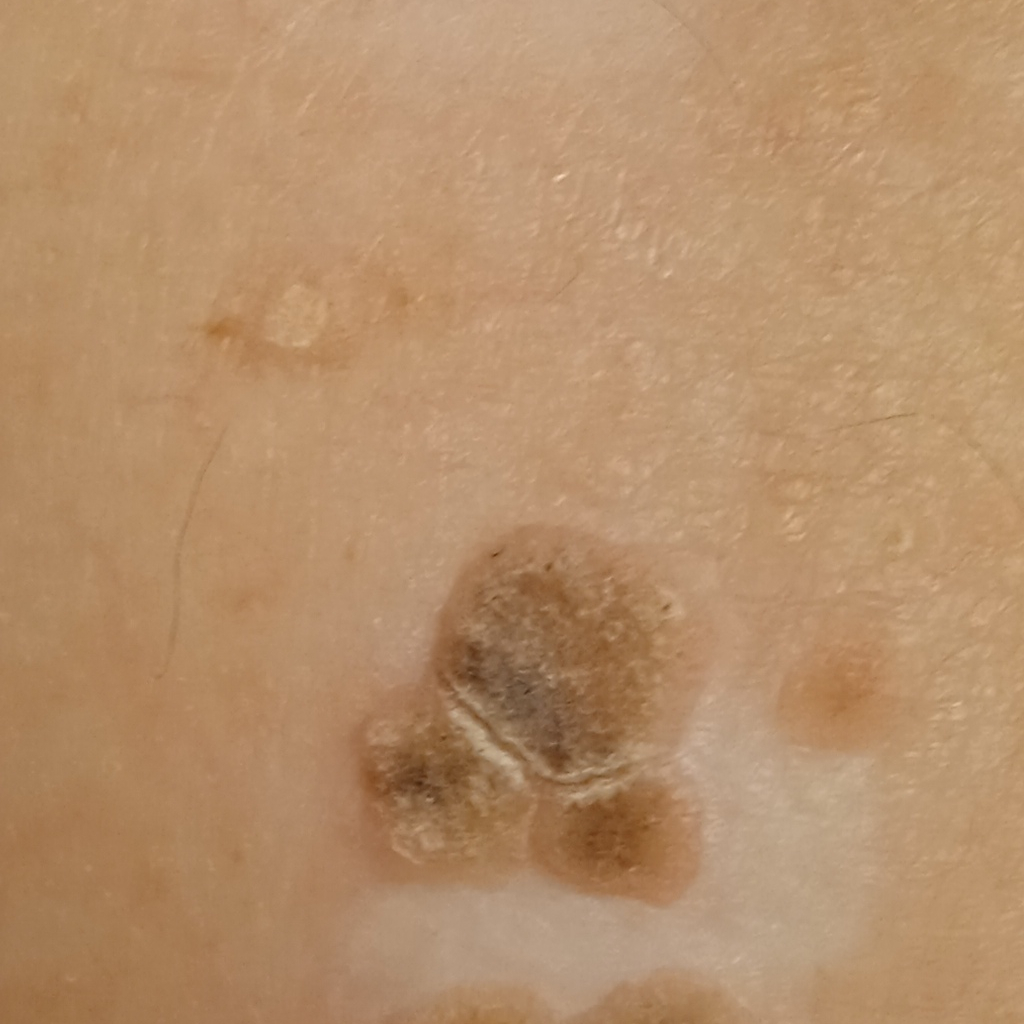<case>
<diagnosis>
<name>seborrheic keratosis</name>
<malignancy>benign</malignancy>
</diagnosis>
</case>